A smartphone photograph of a skin lesion. A patient 55 years of age.
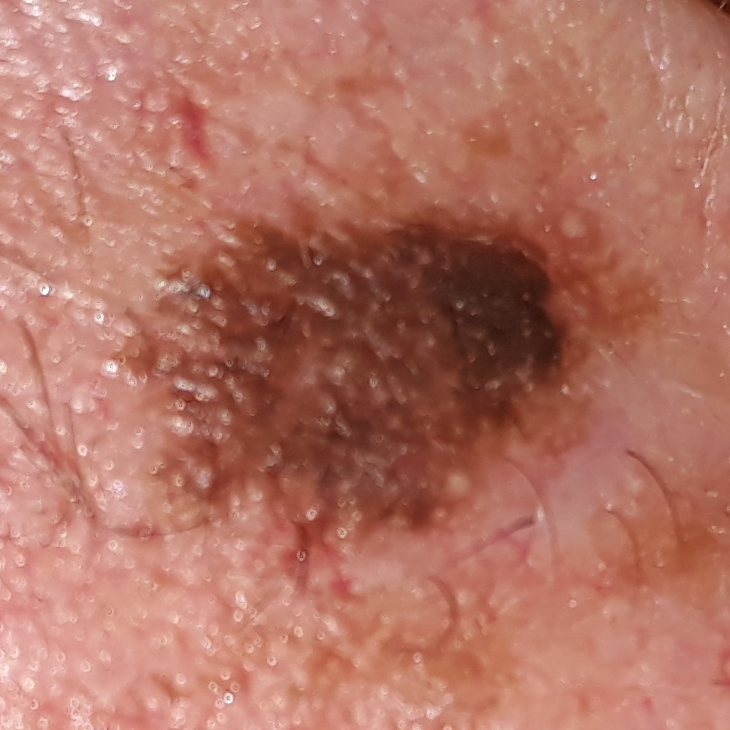reported symptoms: elevation, growth
diagnosis: seborrheic keratosis (clinical consensus)